The patient described the issue as a rash · texture is reported as raised or bumpy · present for more than one year · the arm is involved · this is a close-up image:
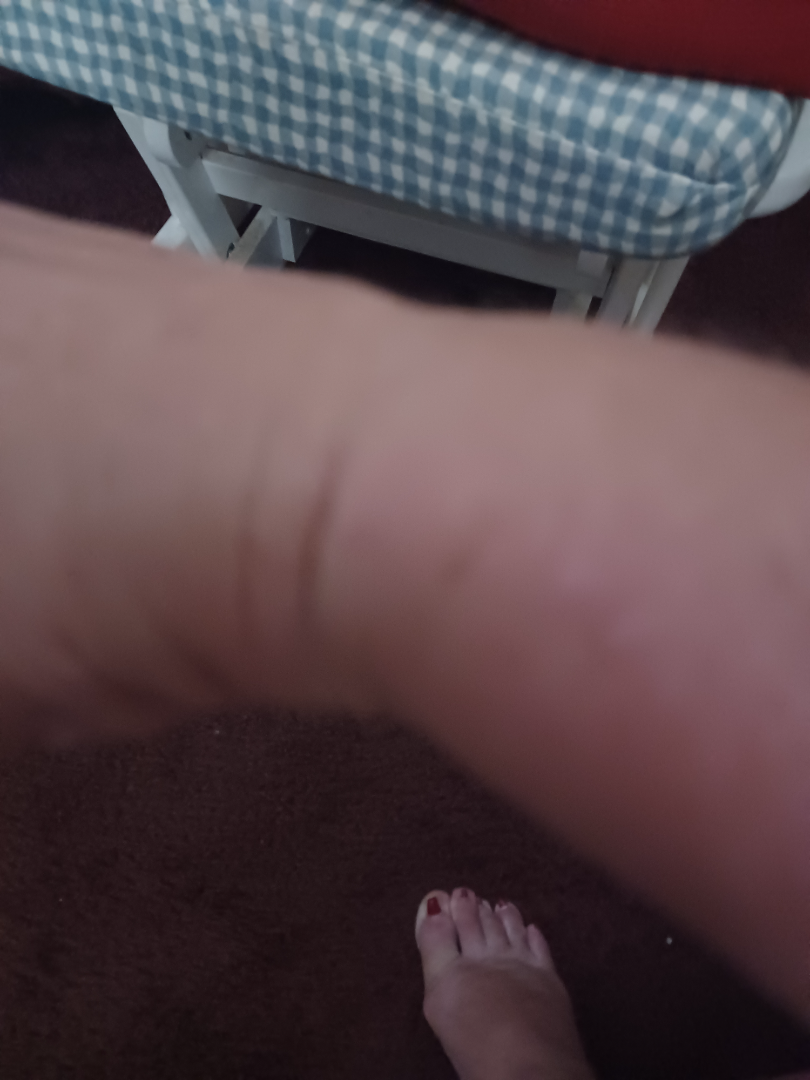Impression: The reviewing dermatologist was unable to assign a differential diagnosis from the image.